This is a close-up image.
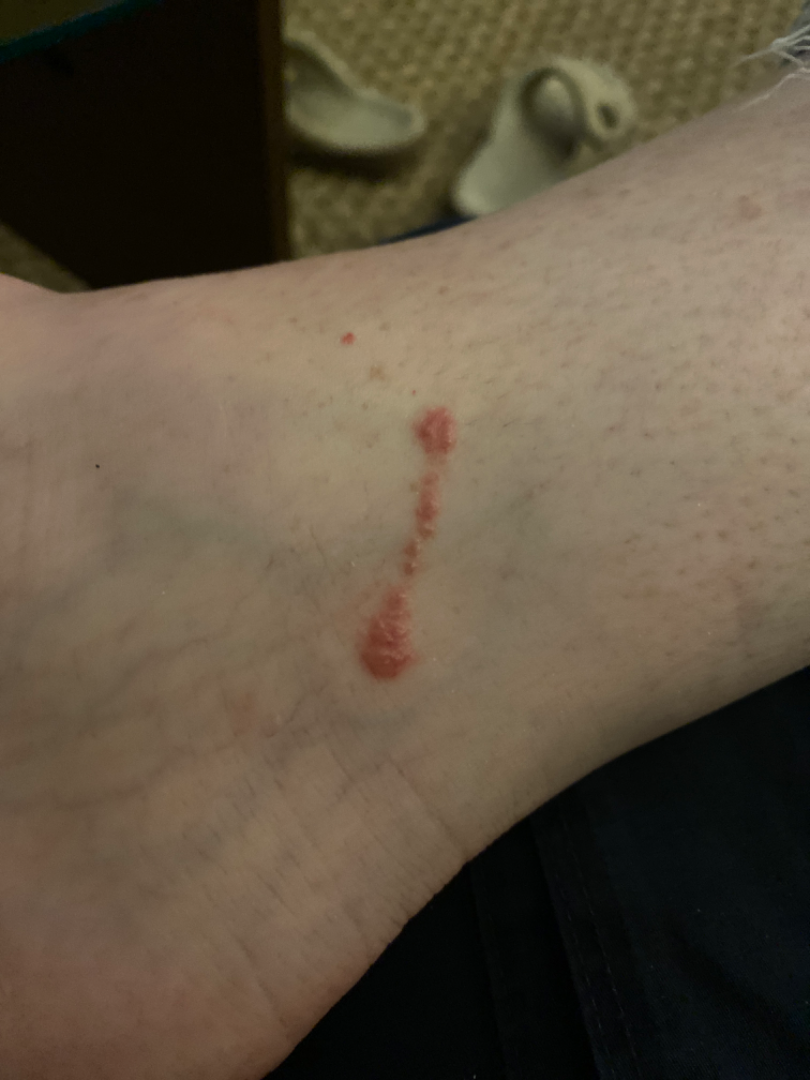Findings:
On dermatologist assessment of the image, consistent with Allergic Contact Dermatitis.